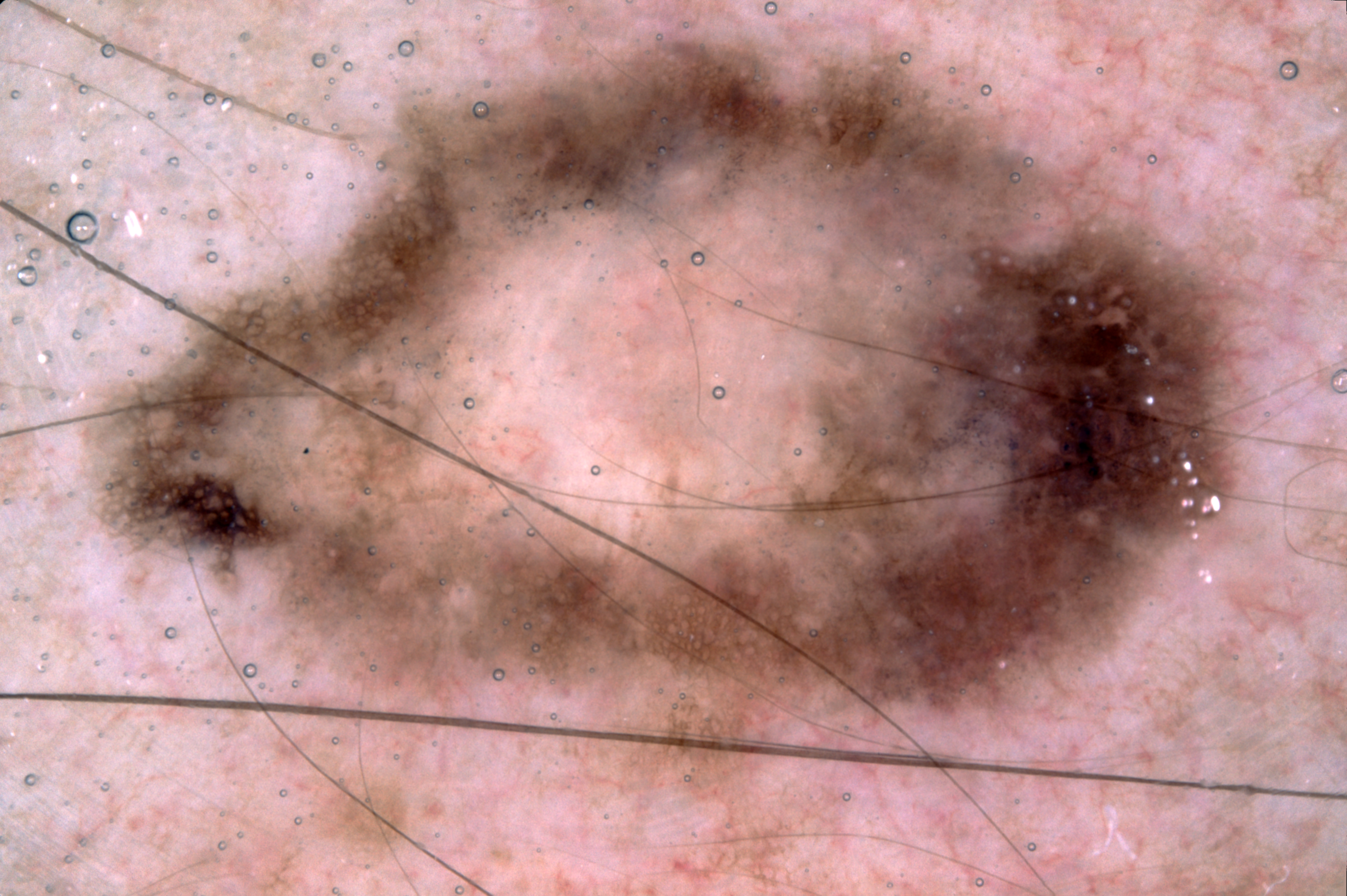A male subject, in their 40s.
A skin lesion imaged with a dermatoscope.
Lesion location: bbox=[95, 35, 1242, 812].
Dermoscopic examination shows pigment network and negative network; no milia-like cysts or streaks.
The lesion covers approximately 53% of the dermoscopic field.
Biopsy-confirmed as a melanoma, a malignant skin lesion.